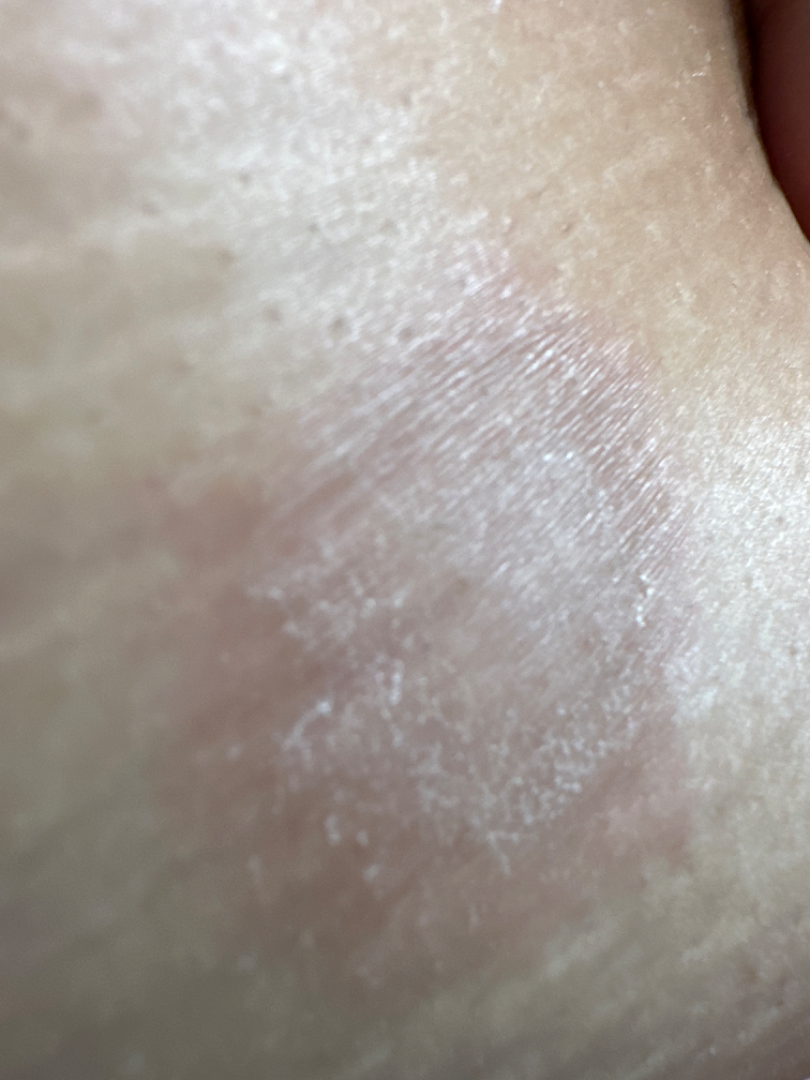FST V. The photo was captured at an angle. On teledermatology review, most consistent with Pityriasis rosea.